A skin lesion imaged with a dermatoscope: 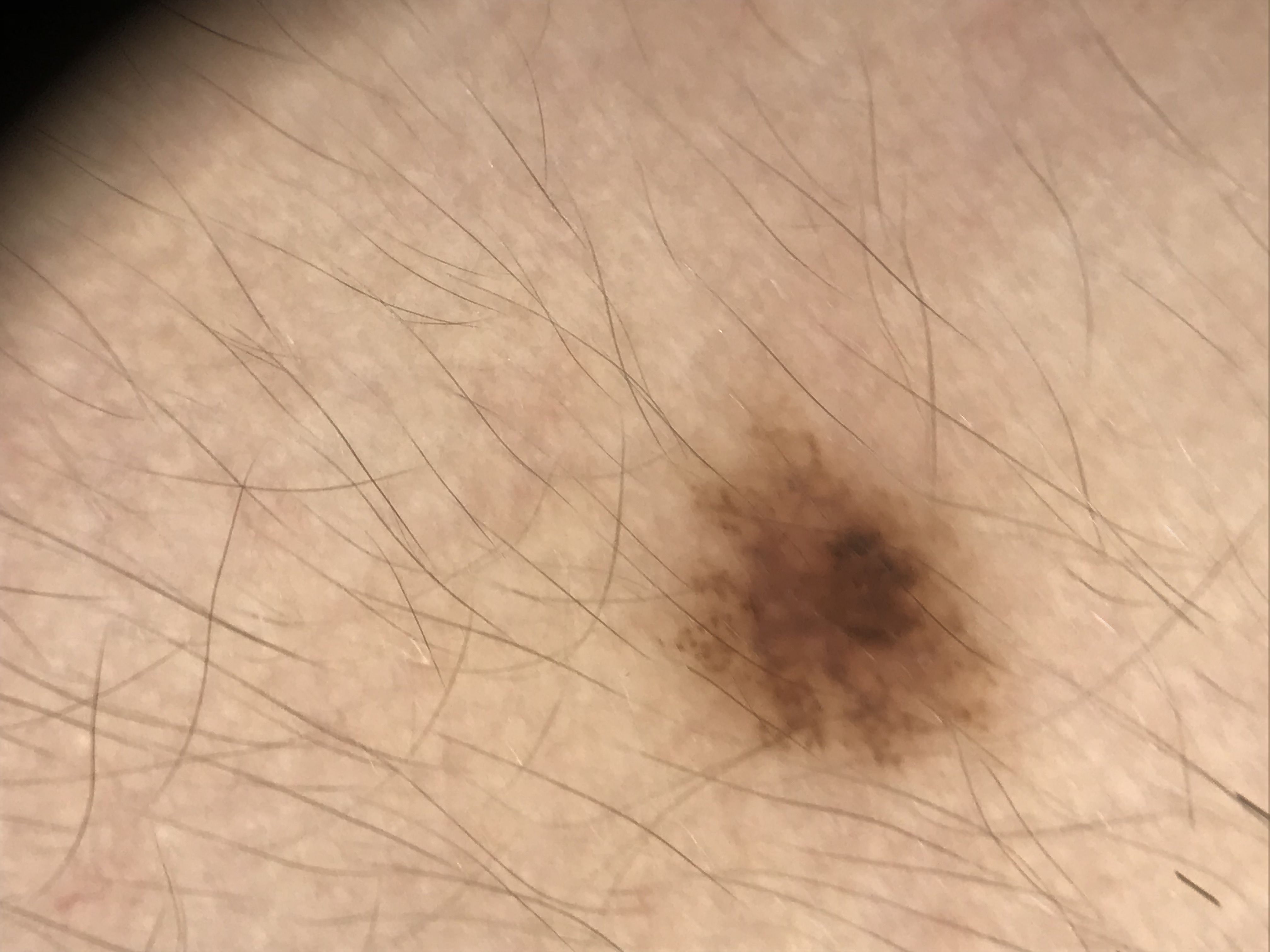Findings:
- assessment · dysplastic junctional nevus (expert consensus)